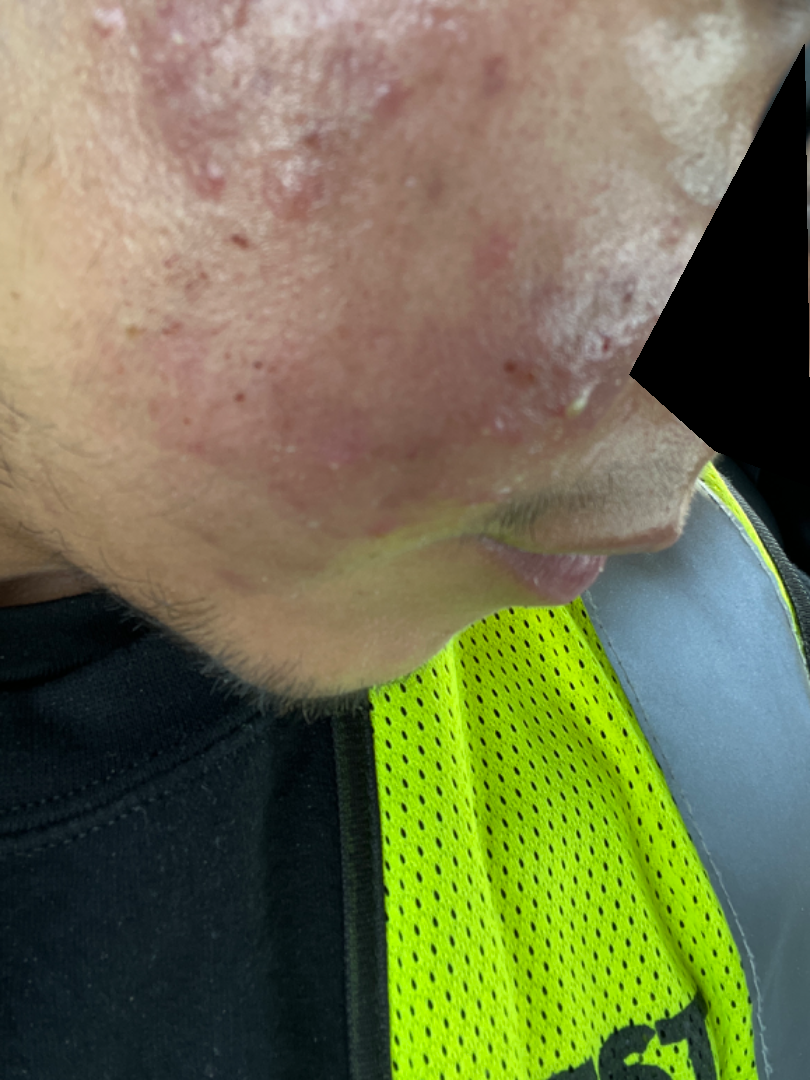History:
The patient is a male aged 18–29. The lesion involves the head or neck. An image taken at an angle.
Impression:
The favored diagnosis is Acne; also raised was Rosacea; less probable is Skin and soft tissue atypical mycobacterial infection.